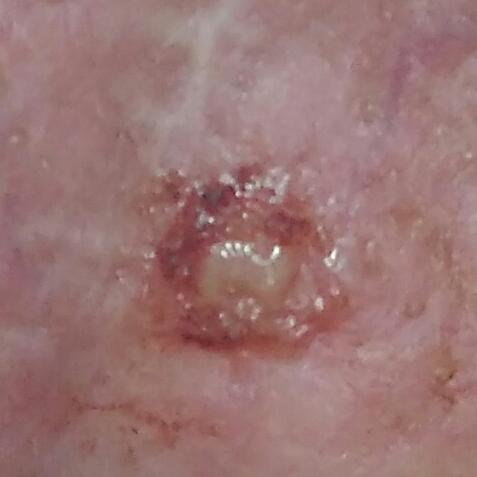{"skin_type": "II", "risk_factors": {"positive": ["prior skin cancer (patient or family)"], "negative": ["alcohol use"]}, "patient": {"age": 52, "gender": "female"}, "image": "clinical photograph", "lesion_location": "the nose", "lesion_size": {"diameter_1_mm": 4.0, "diameter_2_mm": 4.0}, "symptoms": {"present": ["growth", "itching", "elevation", "pain", "bleeding"], "absent": ["change in appearance"]}, "diagnosis": {"name": "basal cell carcinoma", "code": "BCC", "malignancy": "malignant", "confirmation": "histopathology"}}